The patient described the issue as a rash · symptoms reported: bothersome appearance, itching and burning · the lesion involves the leg · FST III; lay graders estimated MST 2 (US pool) or 3 (India pool) · present for about one day · this is a close-up image · the lesion is described as flat — 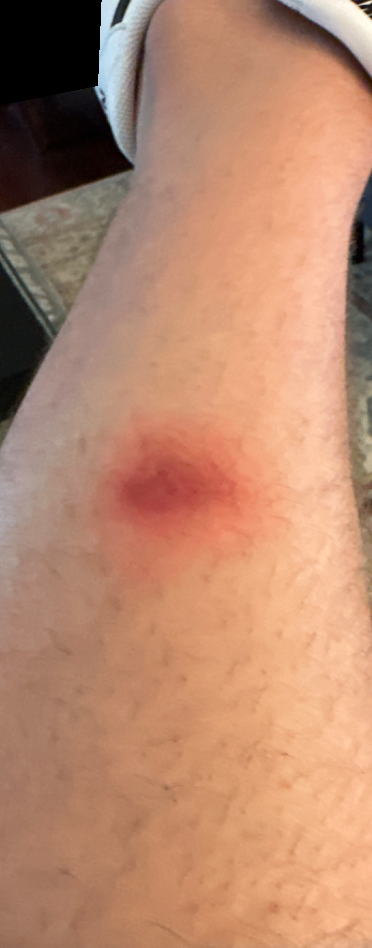A single dermatologist reviewed the case: the leading impression is Erythema nodosum; an alternative is Eczema; also consider Non-specific panniculitis.